A dermoscopic image of a skin lesion.
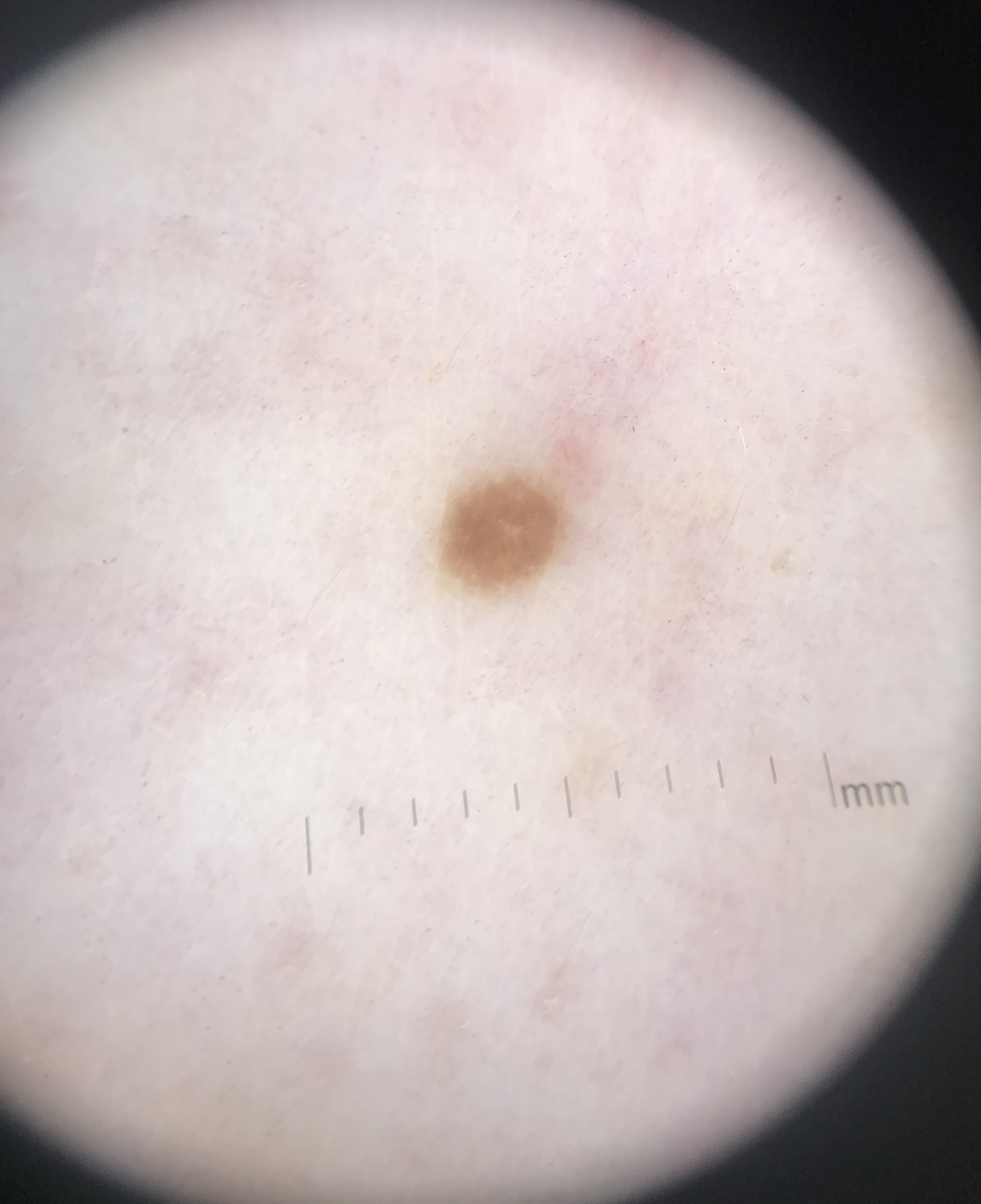Q: What was the diagnostic impression?
A: seborrheic keratosis (expert consensus)